A close-up photograph: 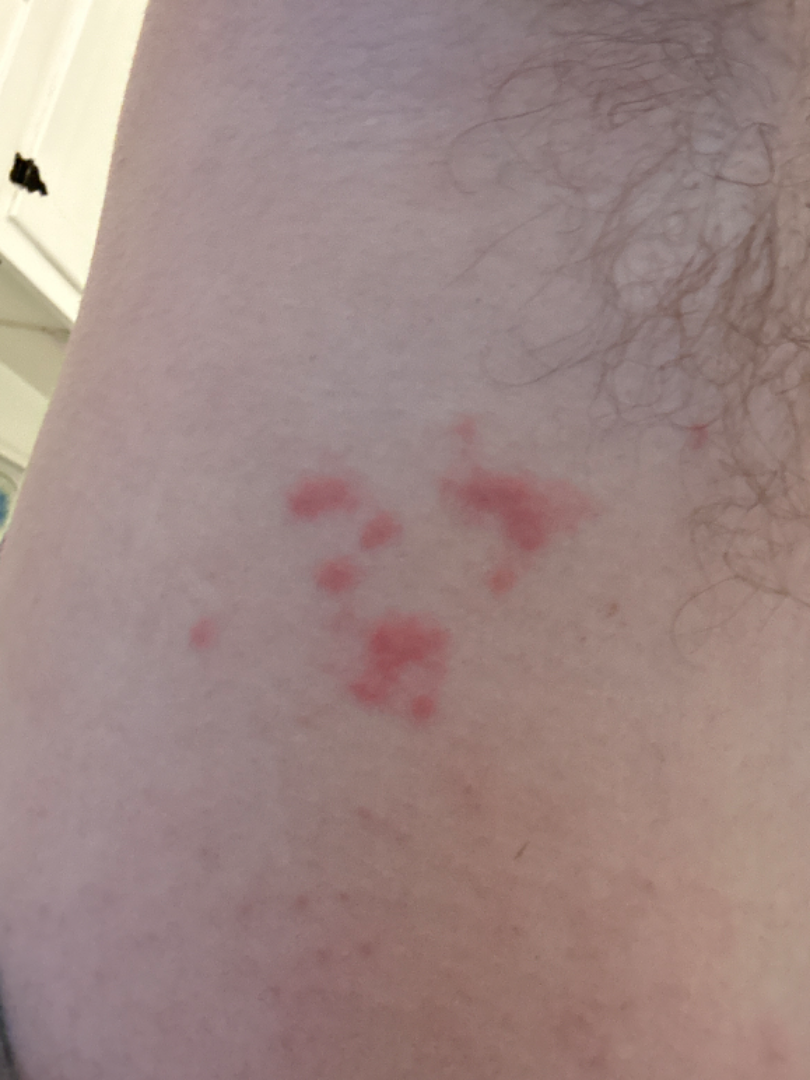The leading consideration is Folliculitis; an alternative is Irritant Contact Dermatitis; also raised was Herpes Simplex.